Collected as part of a research study, without a referral diagnosis.
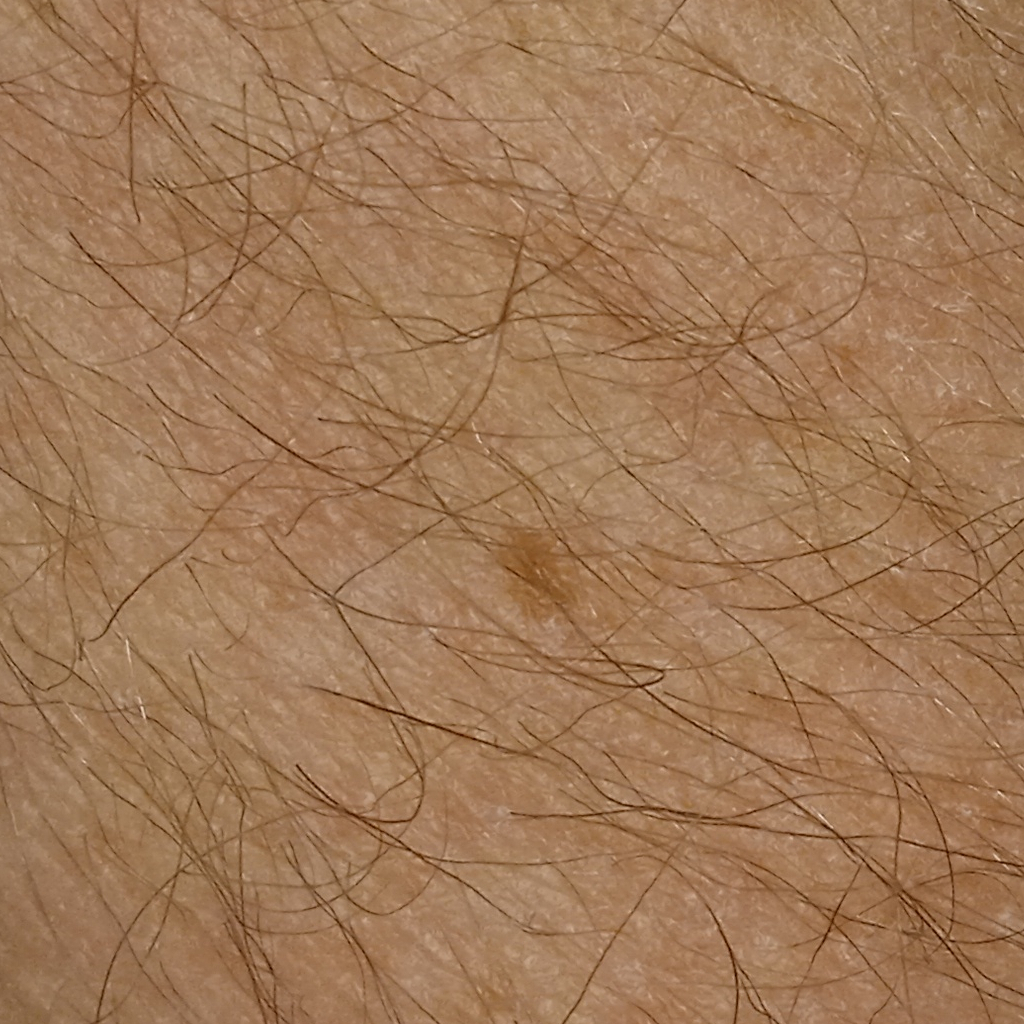| field | value |
|---|---|
| anatomic site | an arm |
| lesion size | 3.4 mm |
| diagnosis | melanocytic nevus (dermatologist consensus) |